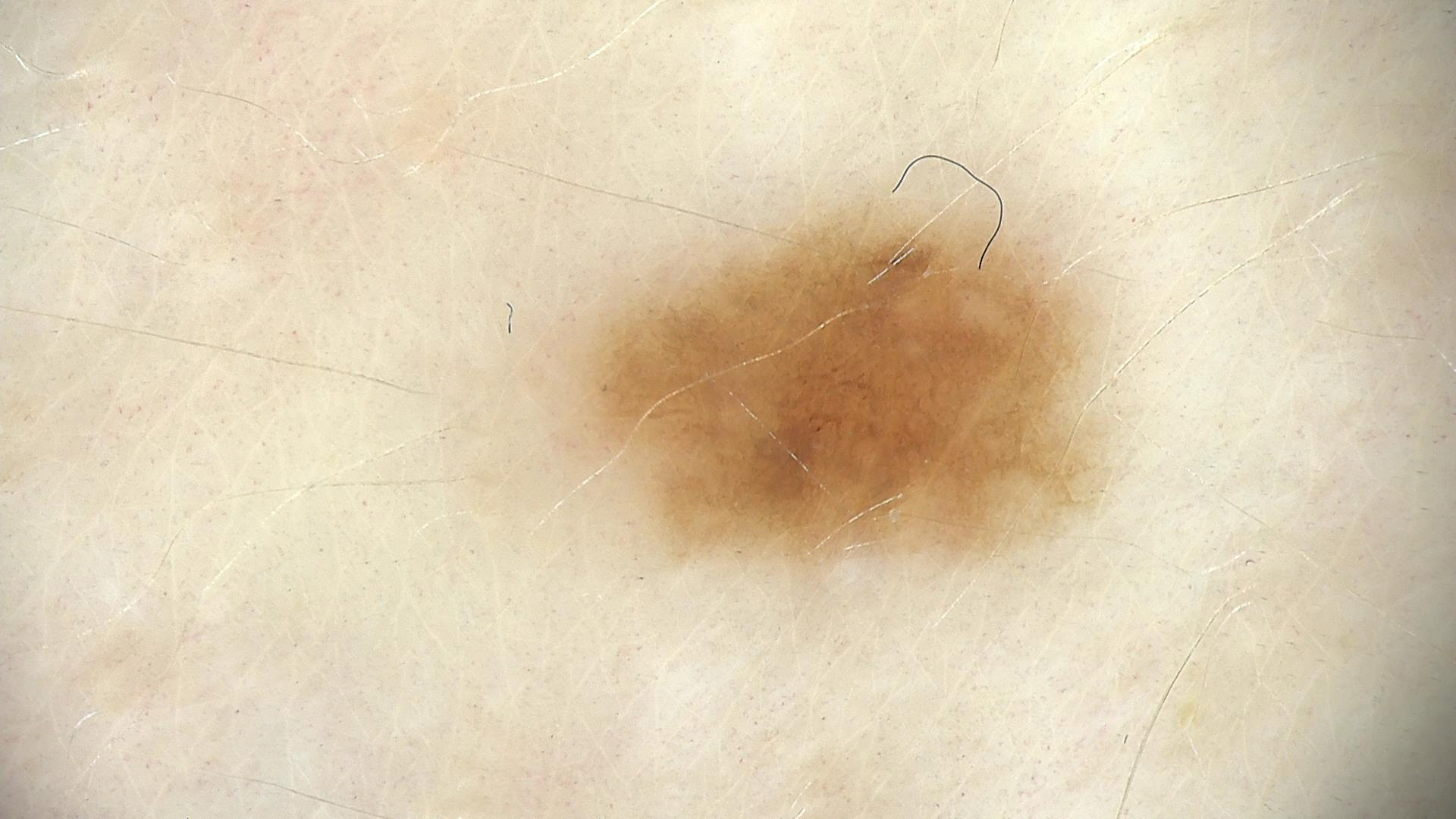A dermoscopy image of a single skin lesion.
The diagnosis was a dysplastic junctional nevus.